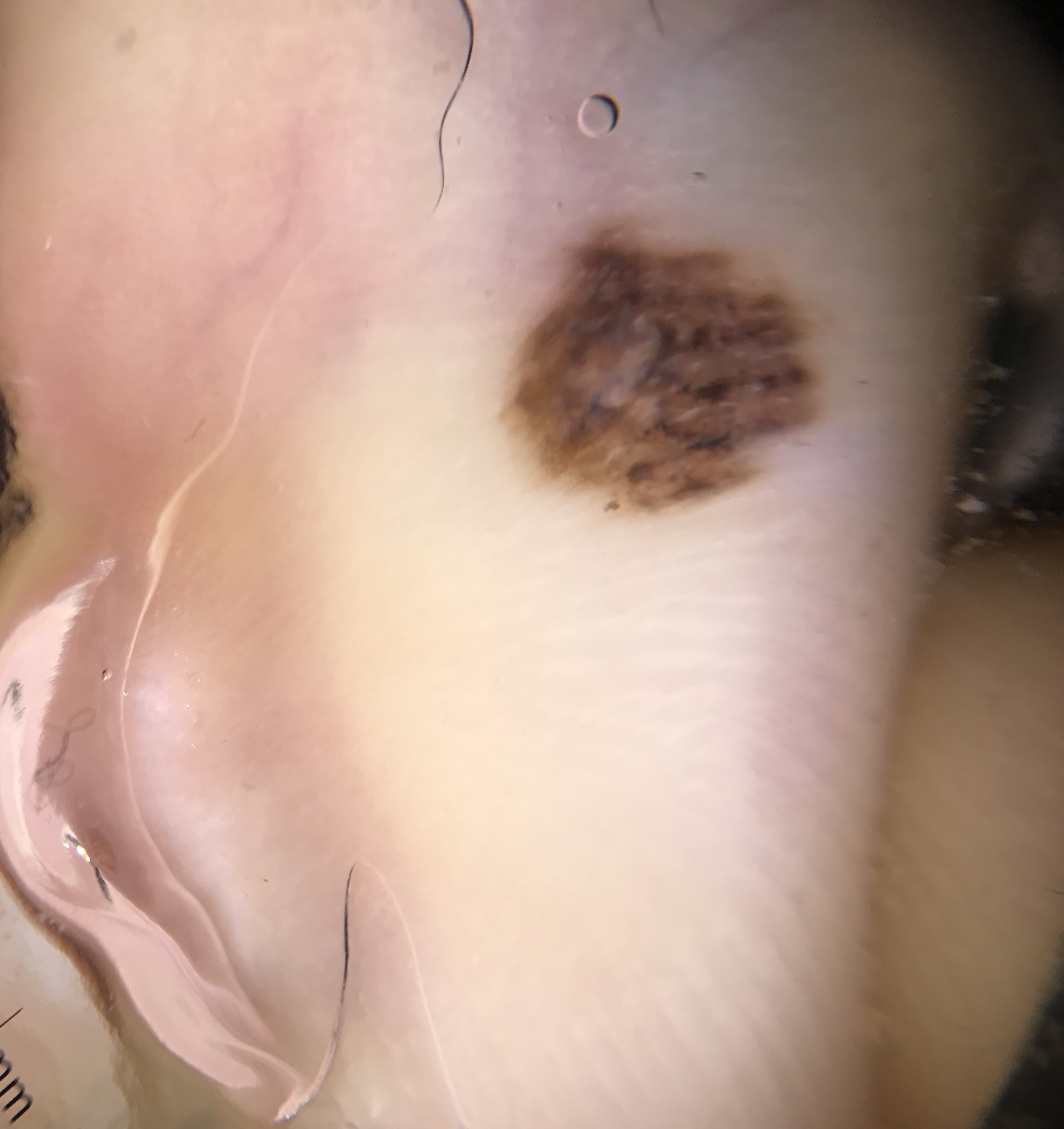Diagnosed as an acral dysplastic compound nevus.